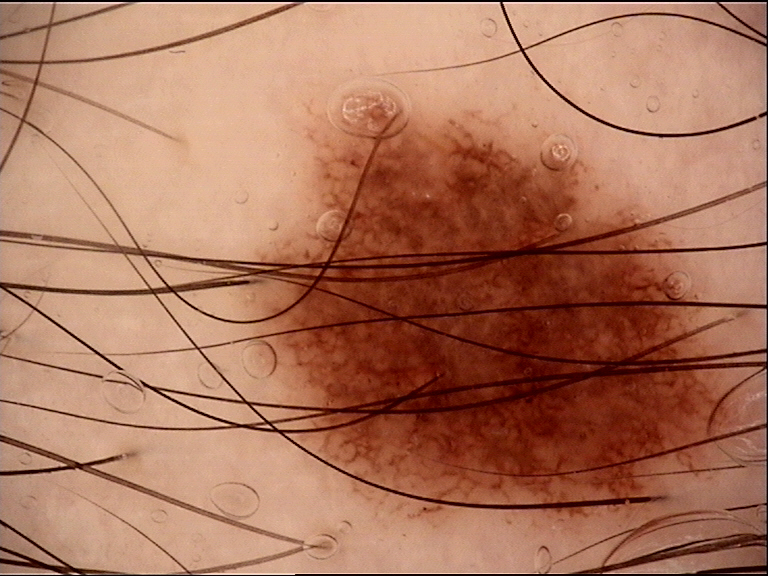Diagnosed as a dysplastic junctional nevus.